Dermoscopy of a skin lesion:
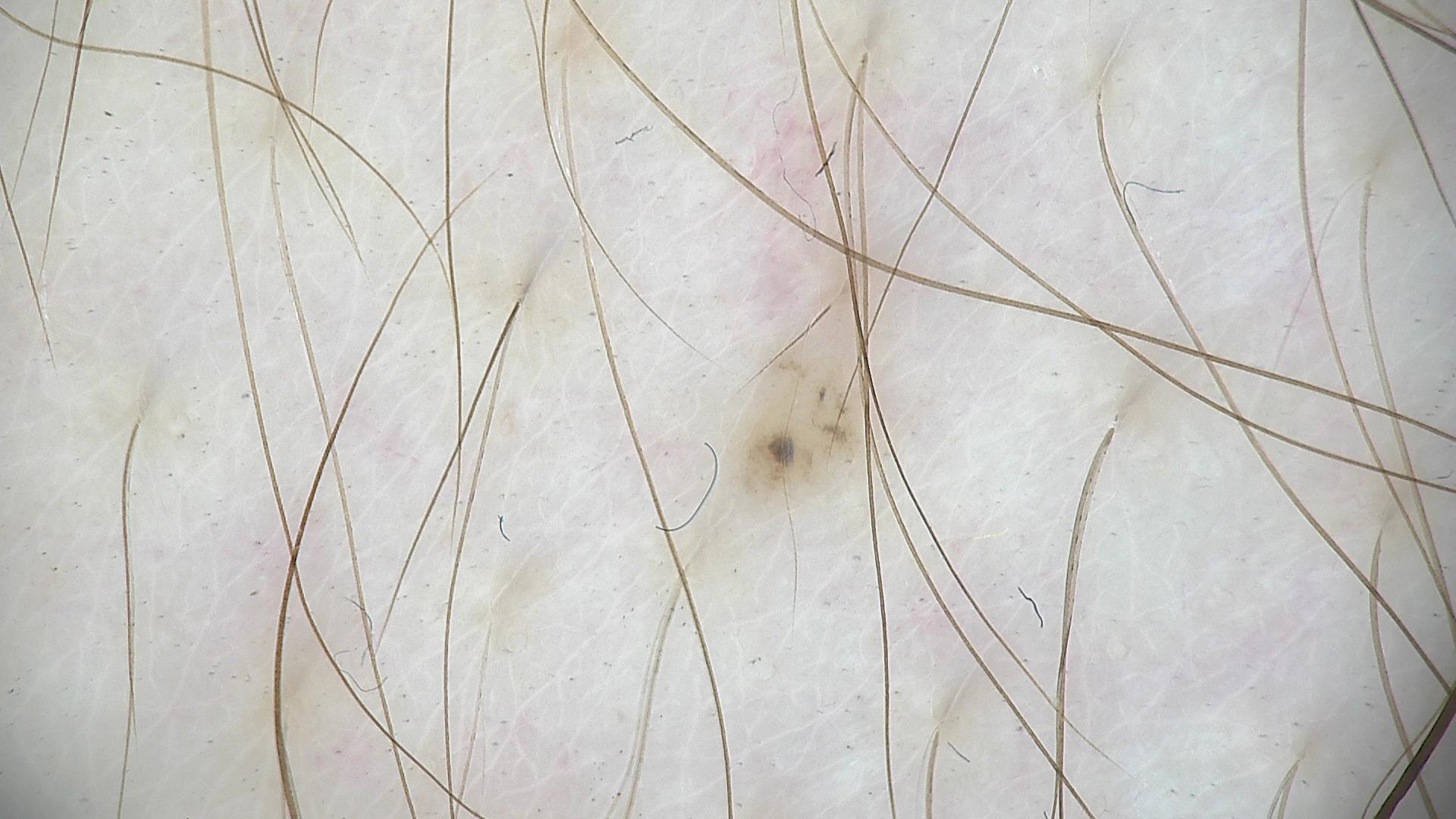Conclusion: Diagnosed as a dysplastic junctional nevus.